Texture is reported as flat · the affected area is the leg, arm and back of the hand · the patient described the issue as a rash · the condition has been present for about one day · the photo was captured at an angle: 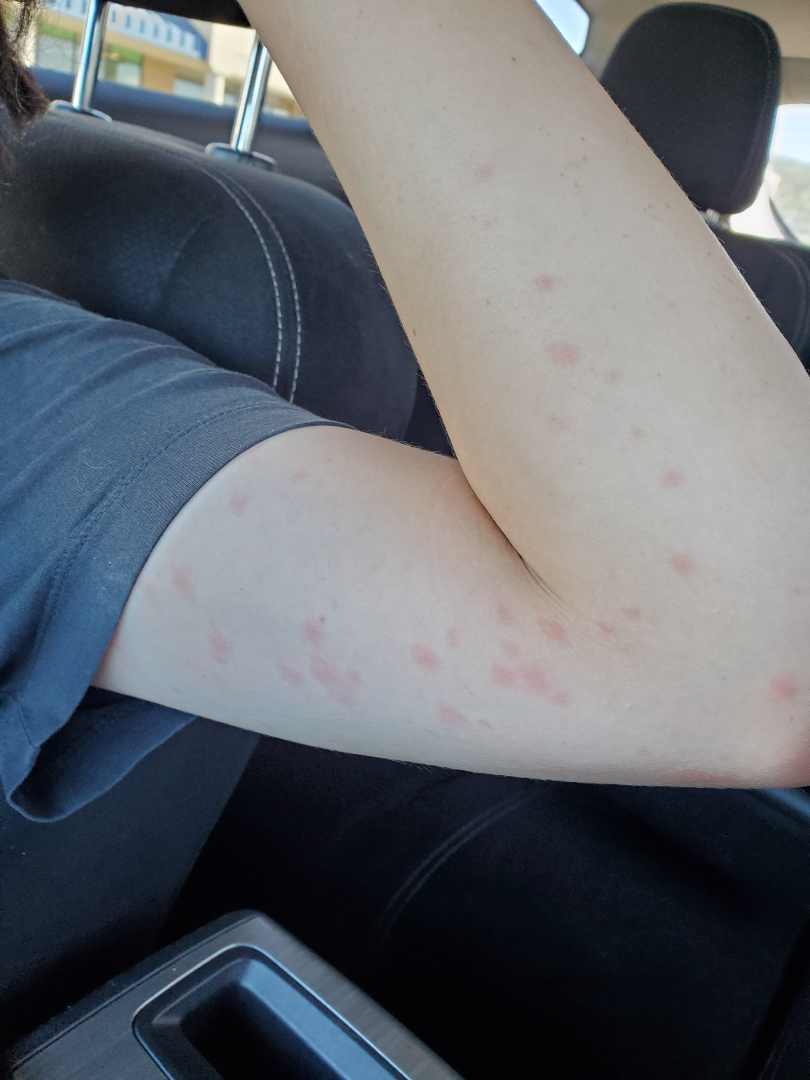| feature | finding |
|---|---|
| assessment | not assessable |